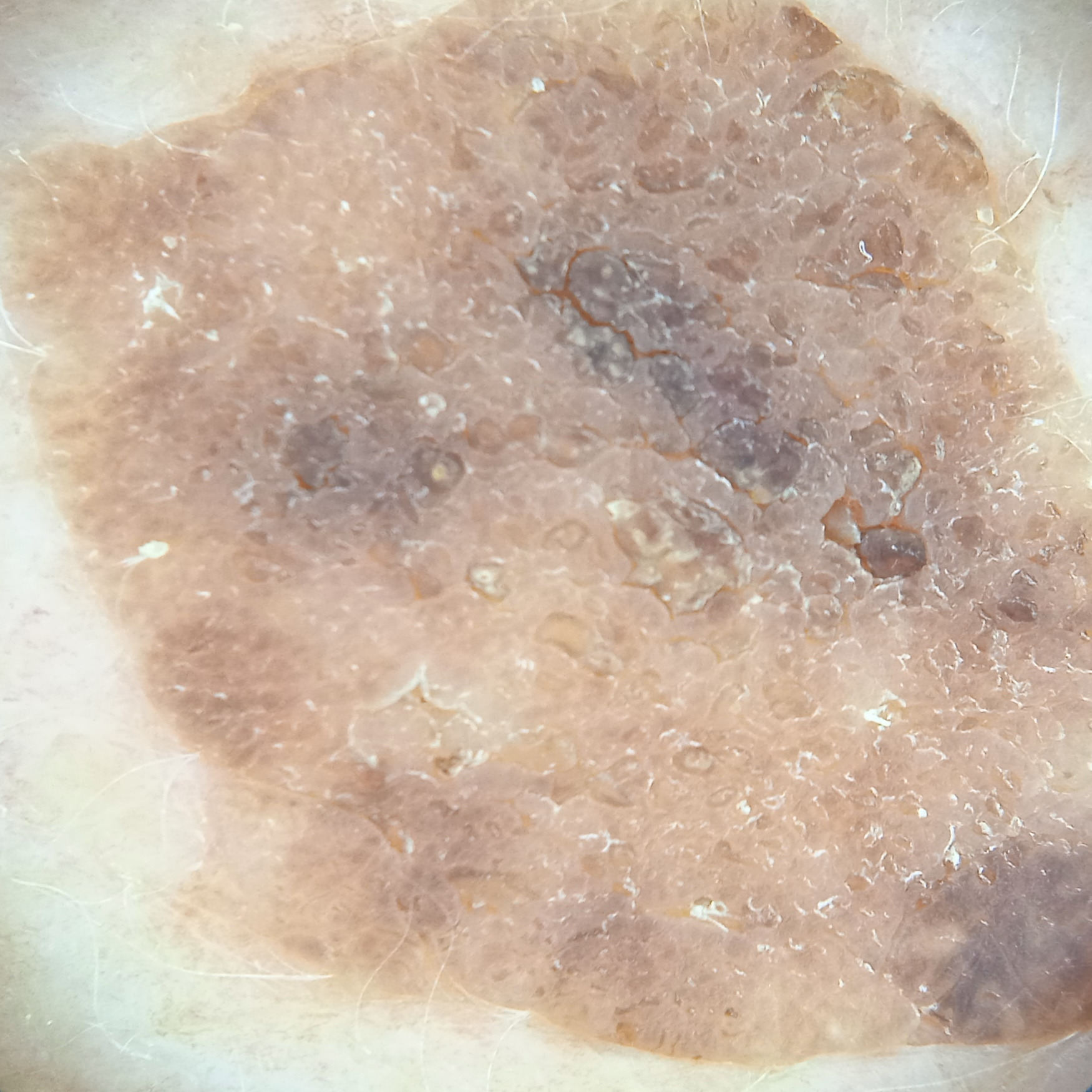Summary: Imaged for a research study, with no referral diagnosis recorded. The patient says their skin tans without first burning. The patient describes having numerous moles. A female subject 78 years of age. The lesion involves the back. The lesion measures approximately 15.7 mm. Assessment: The diagnostic impression was a seborrheic keratosis.